Self-categorized by the patient as a rash, the lesion is associated with itching, this image was taken at an angle, the contributor is a female aged 18–29, lay reviewers estimated Monk Skin Tone 2 or 3 (two reviewer pools), the patient reports the lesion is raised or bumpy:
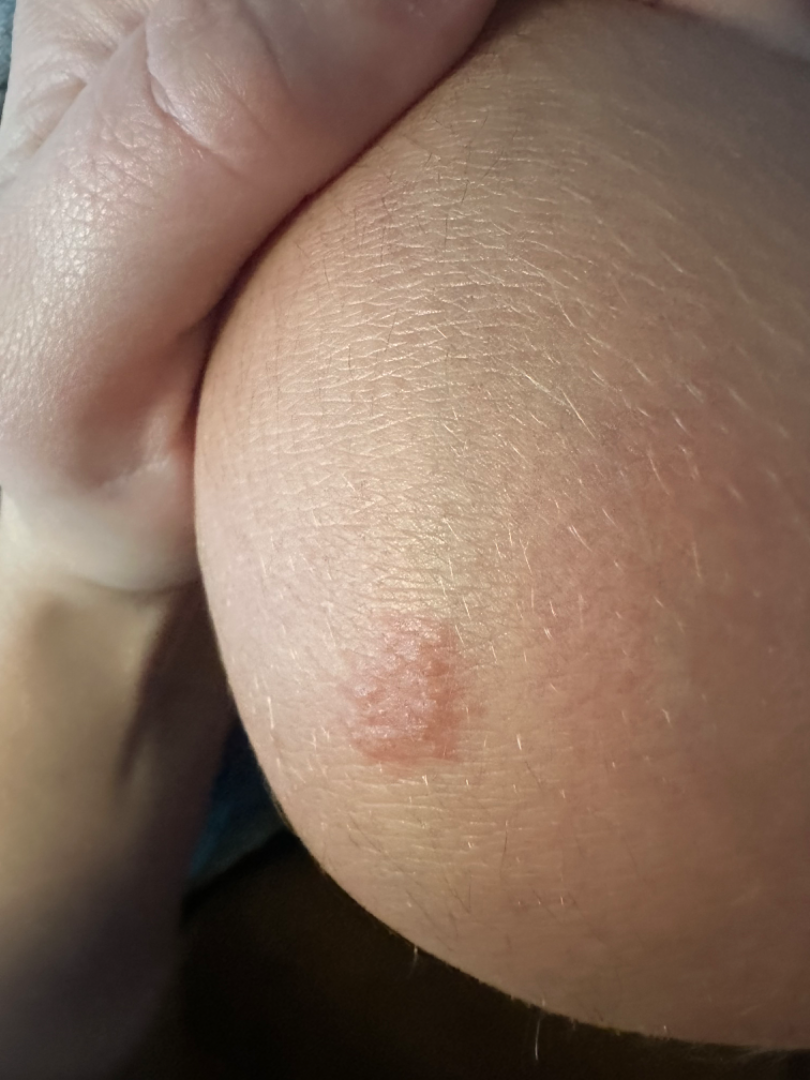Q: Could the case be diagnosed?
A: not assessable